Dermoscopy of a skin lesion.
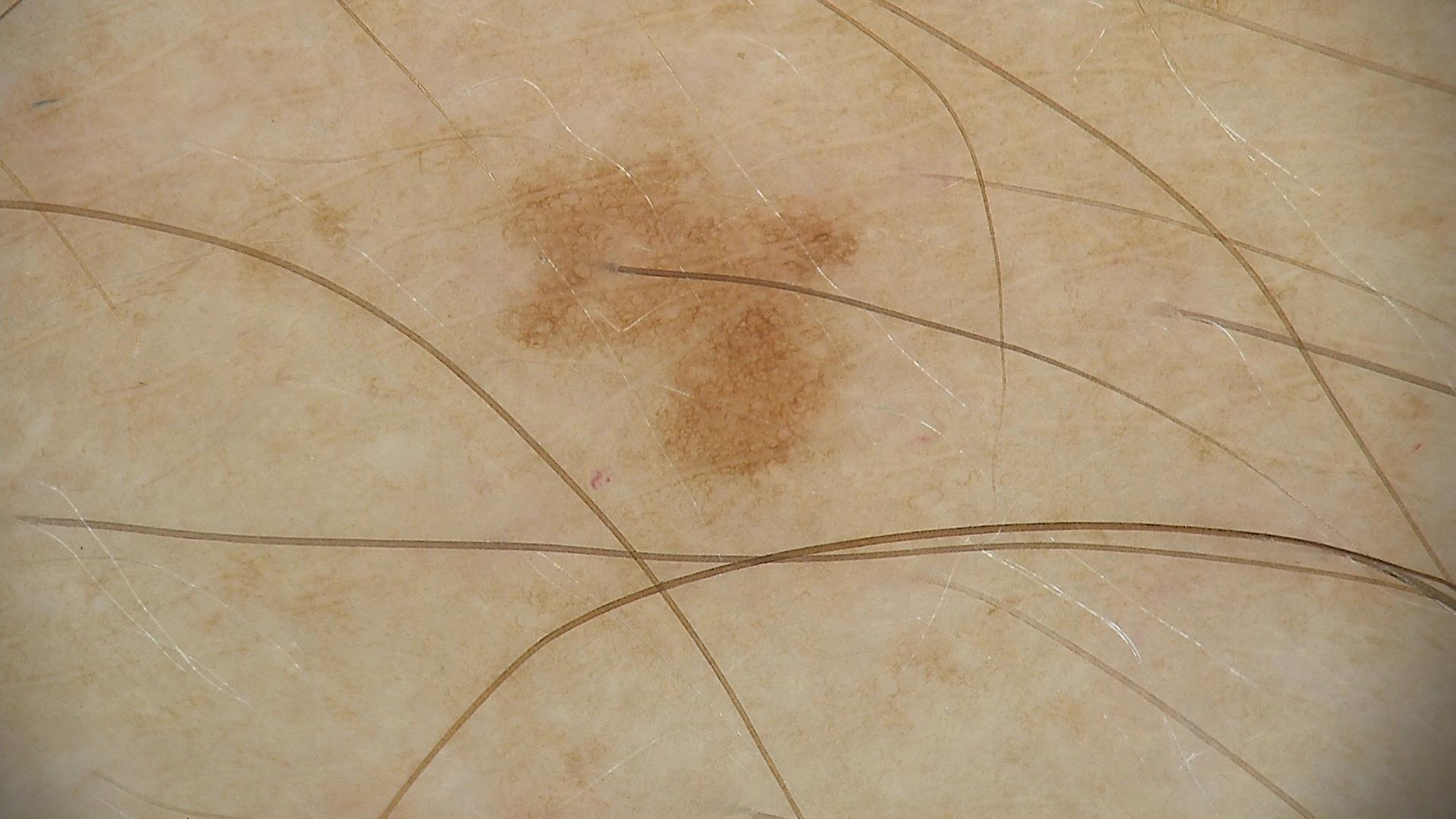lesion type — banal
label — junctional nevus (expert consensus)